A close-up photograph: 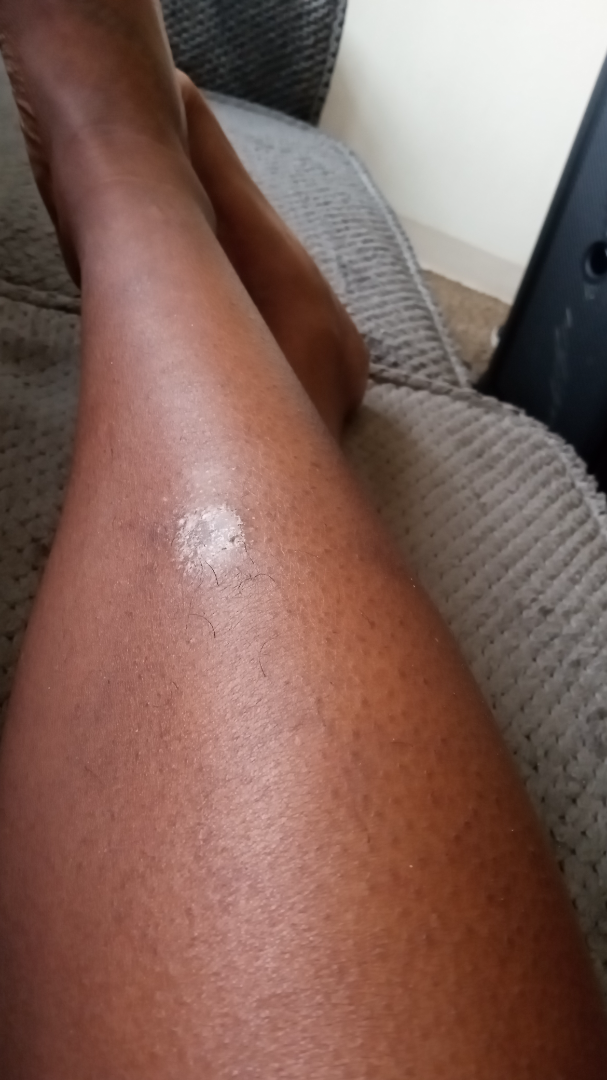Review: Diagnostic features were not clearly distinguishable in this photograph.